A female subject in their mid-50s; a clinical photograph of a skin lesion:
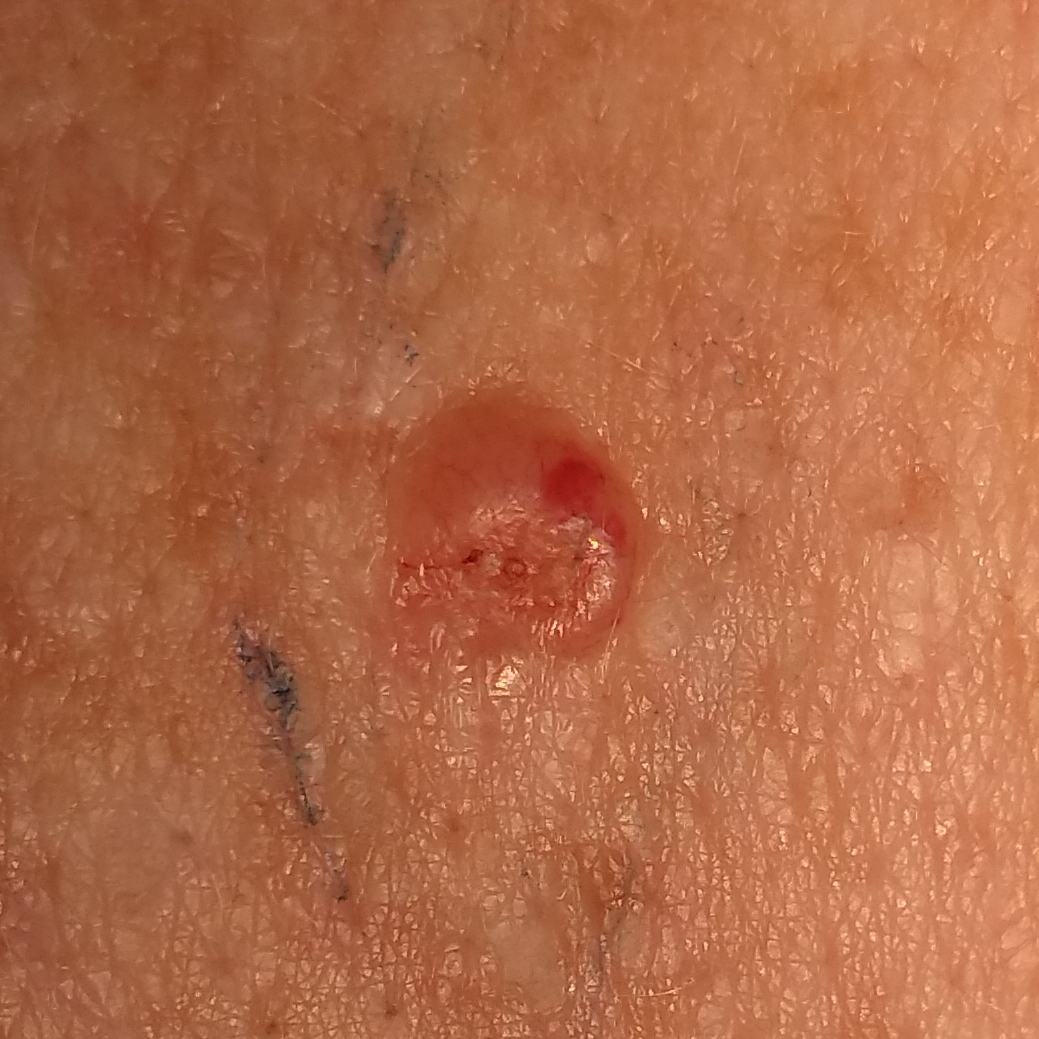Notes:
- symptoms · elevation
- pathology · basal cell carcinoma (biopsy-proven)